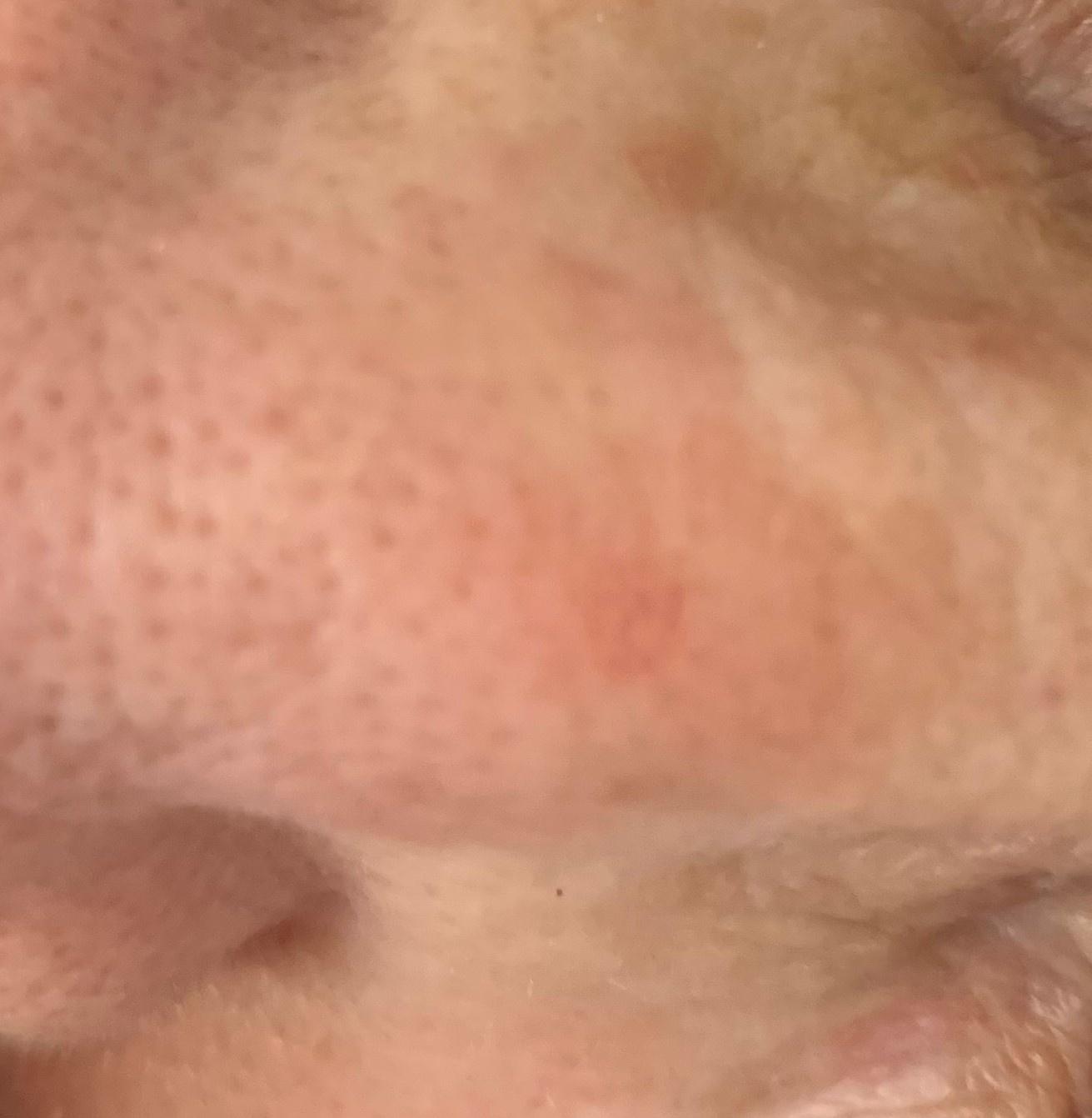Q: What is the diagnosis?
A: Solar or actinic keratosis (clinical impression)